A clinical photo of a skin lesion taken with a smartphone. A subject aged 70: 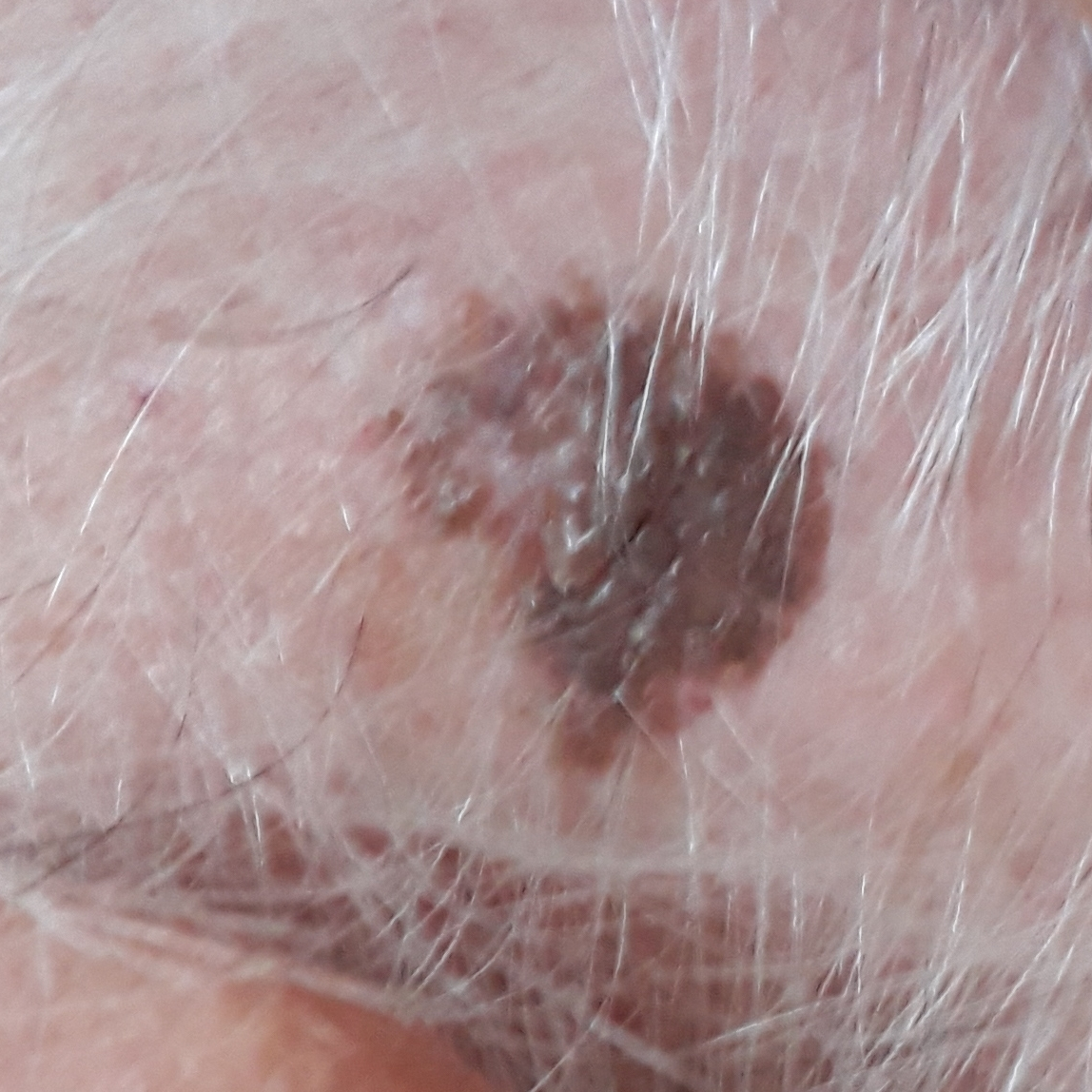anatomic site = the face, patient-reported symptoms = none reported, diagnosis = seborrheic keratosis (clinical consensus).